A clinical photograph showing a skin lesion · a male subject age 68:
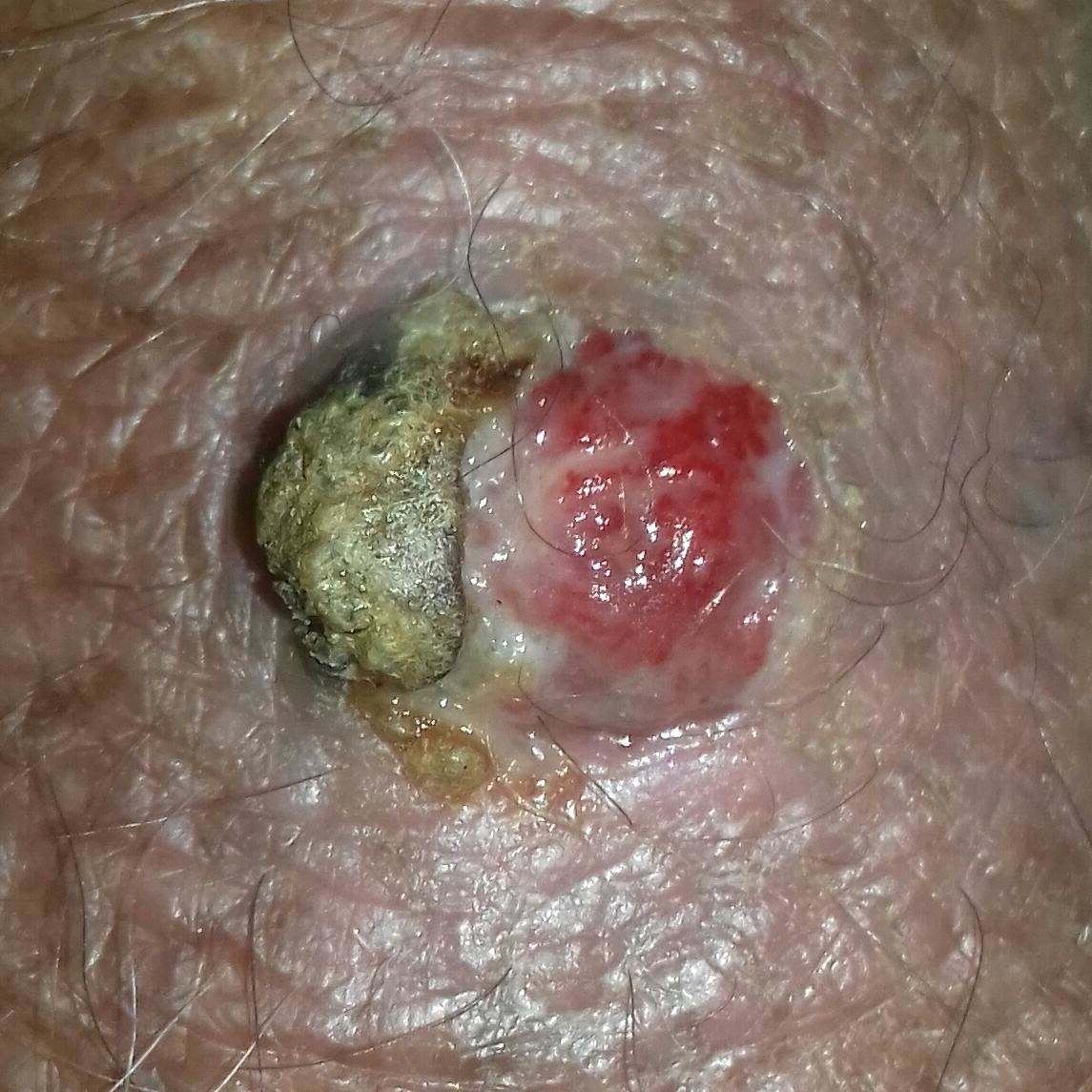The lesion is on a forearm. On biopsy, the diagnosis was a malignant lesion — a squamous cell carcinoma.